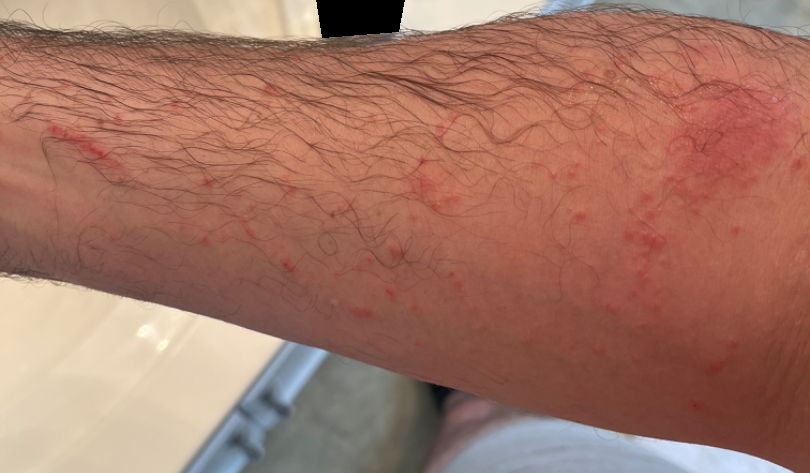The condition could not be reliably identified from the image. The lesion involves the head or neck, leg and arm. The lesion is described as rough or flaky, raised or bumpy and fluid-filled. Male patient, age 30–39. The photograph was taken at an angle. Reported duration is less than one week.